A dermatoscopic image of a skin lesion: 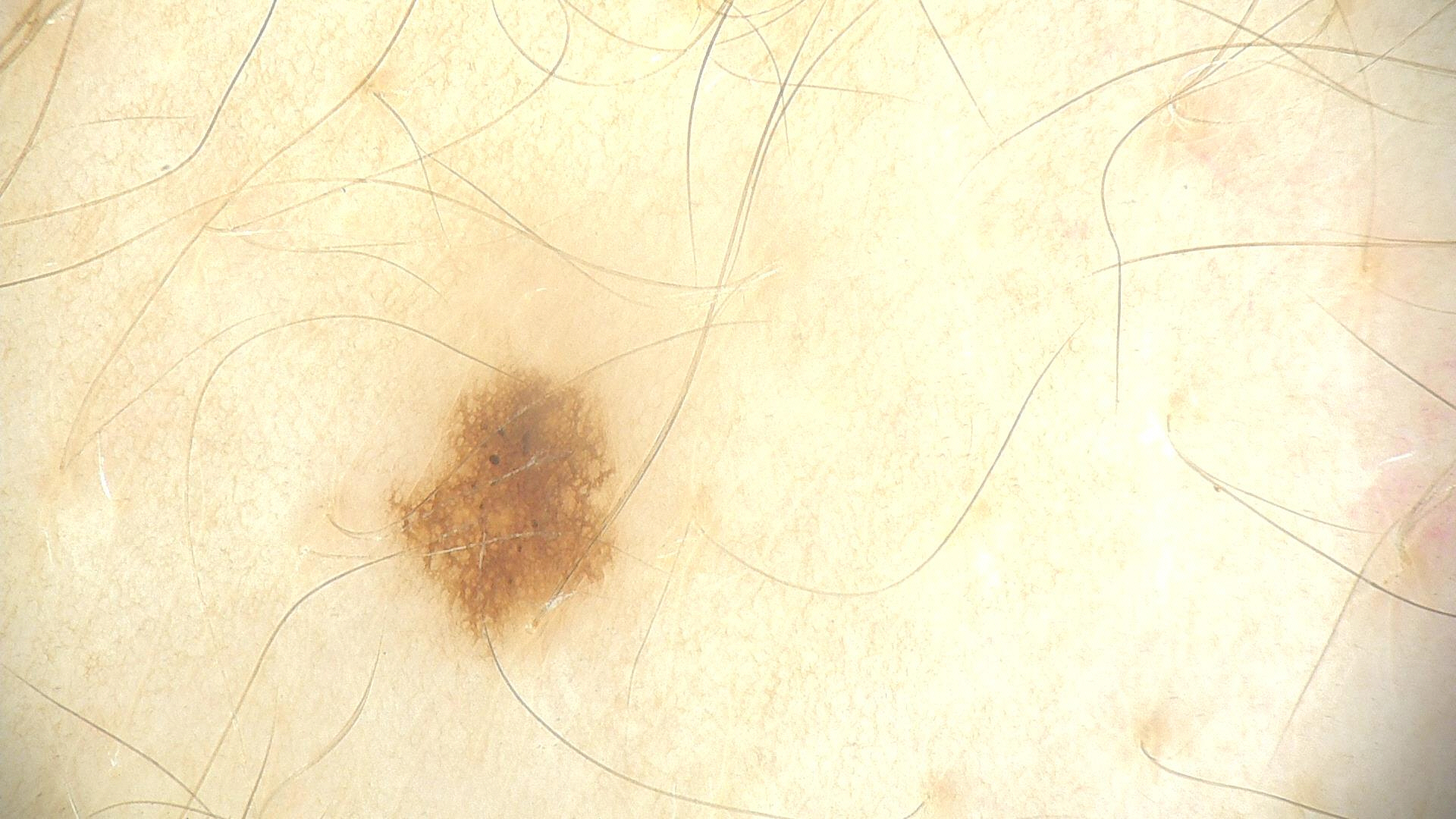| feature | finding |
|---|---|
| diagnosis | dysplastic junctional nevus (expert consensus) |